A dermoscopic close-up of a skin lesion.
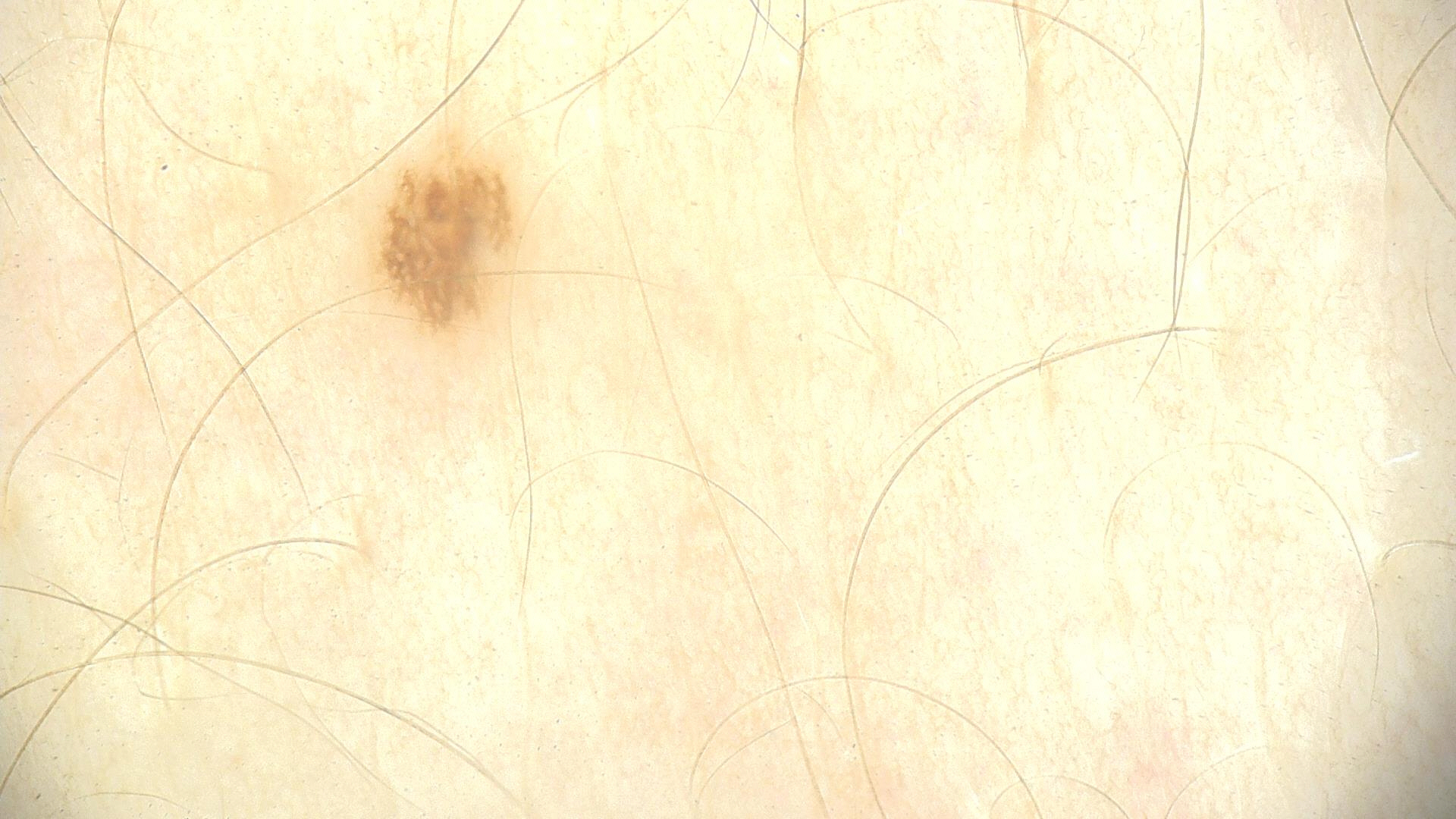Q: What is the diagnosis?
A: dysplastic junctional nevus (expert consensus)